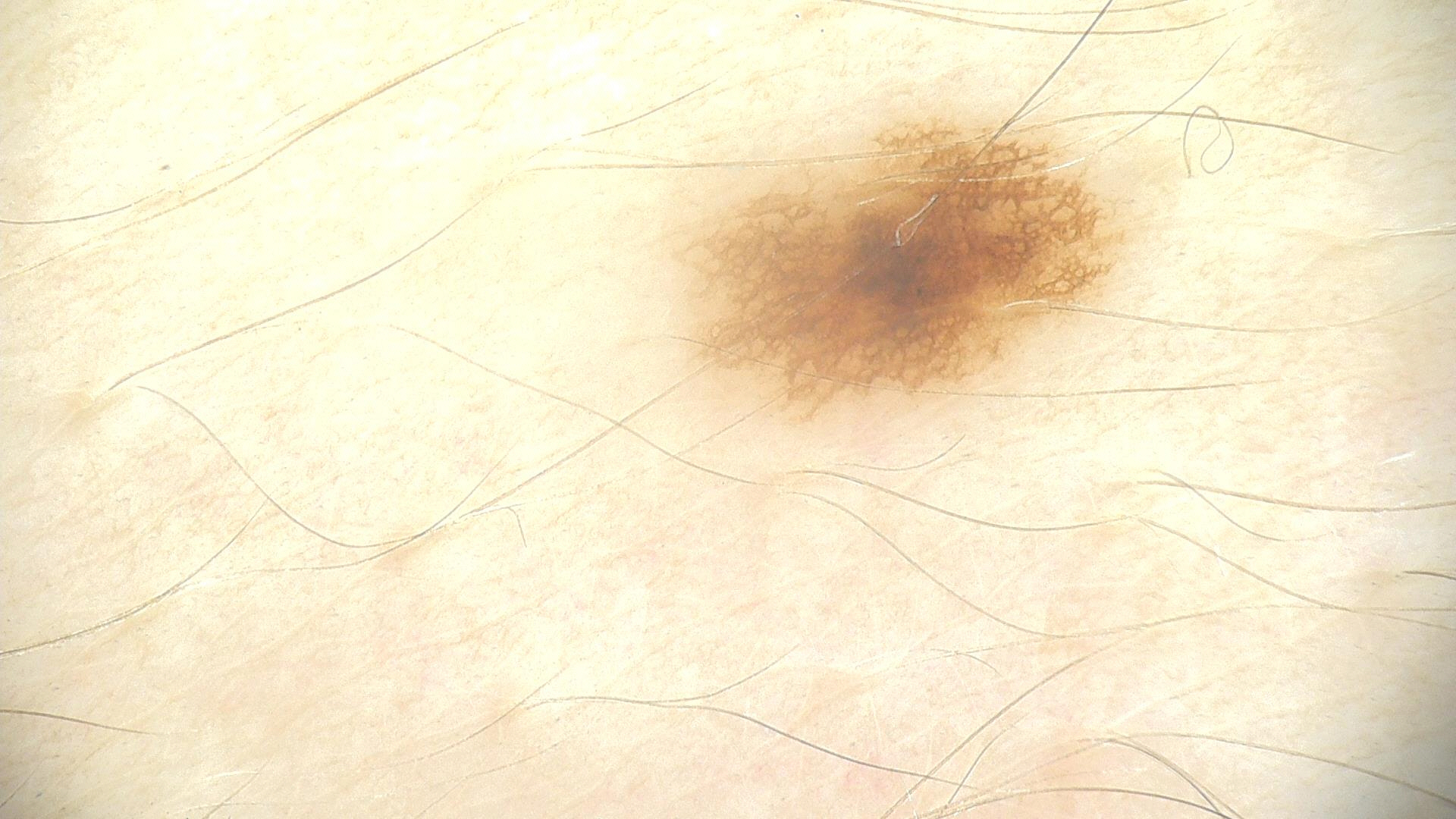  diagnosis:
    name: dysplastic junctional nevus
    code: jd
    malignancy: benign
    super_class: melanocytic
    confirmation: expert consensus